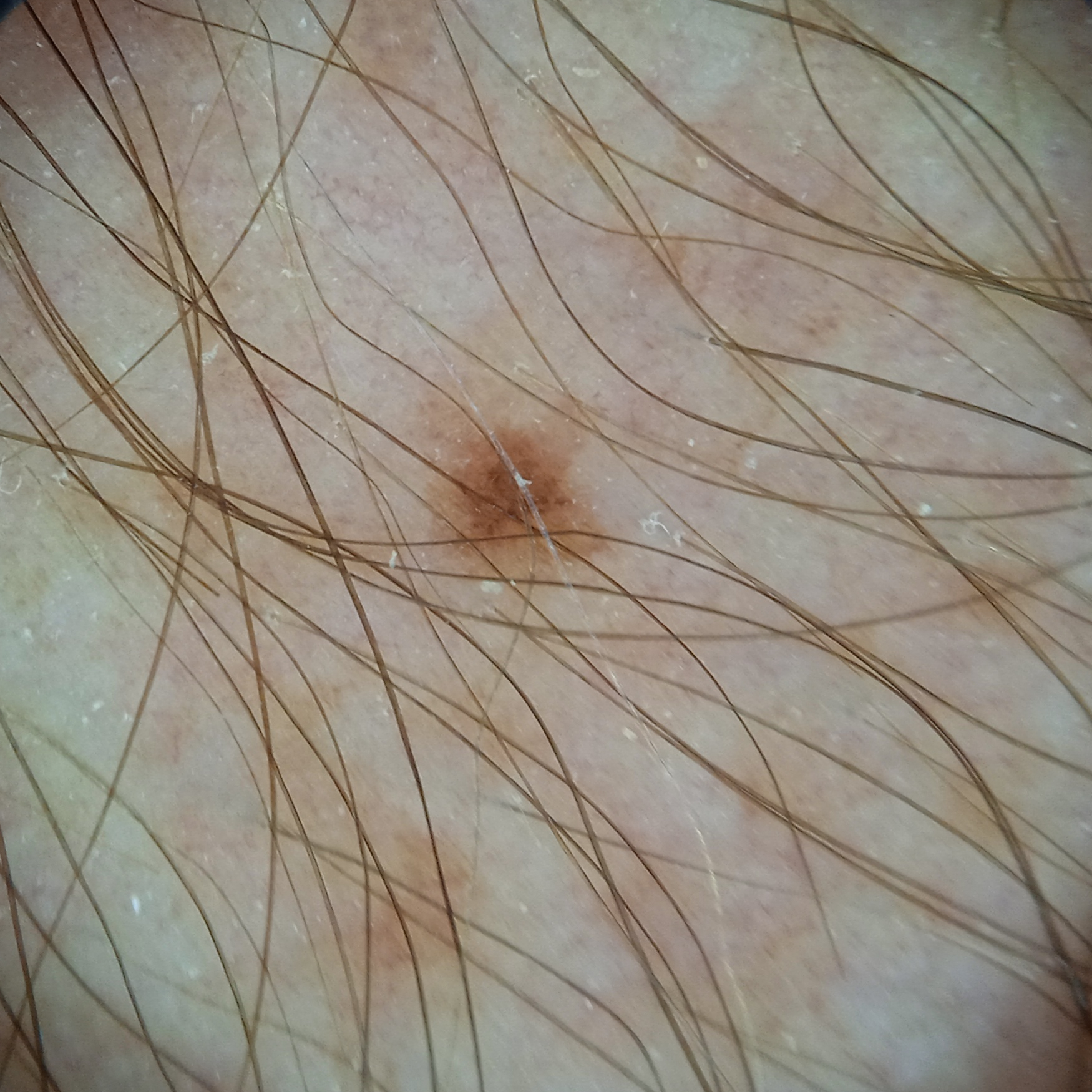Summary:
The patient describes having few moles overall. The patient says their skin reddens with sun exposure. Acquired for a research image collection, with no referral diagnosis. On a questionnaire the patient reported a personal history of skin cancer, a personal history of cancer, no immunosuppression, and no family history of skin cancer. Dermoscopy of a skin lesion. A male patient aged 76. The lesion is located on an arm. The lesion measures approximately 8.2 mm.
Conclusion:
The diagnostic impression was a melanocytic nevus.